A clinical photograph showing a skin lesion · a male subject aged 77 — 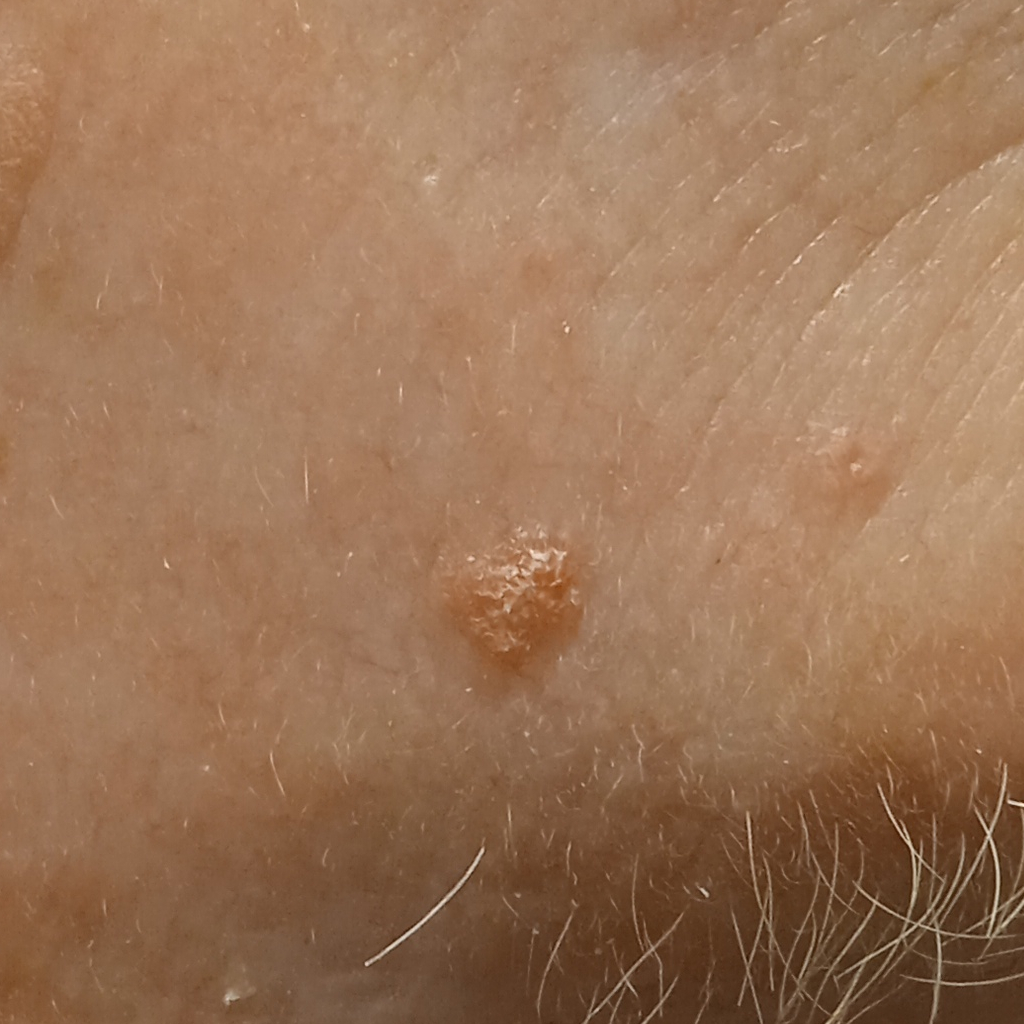Q: Lesion size?
A: 4.3 mm
Q: What was the diagnosis?
A: actinic keratosis (dermatologist consensus)